The lesion involves the front of the torso and back of the torso · this image was taken at an angle · the patient is a female aged 30–39: 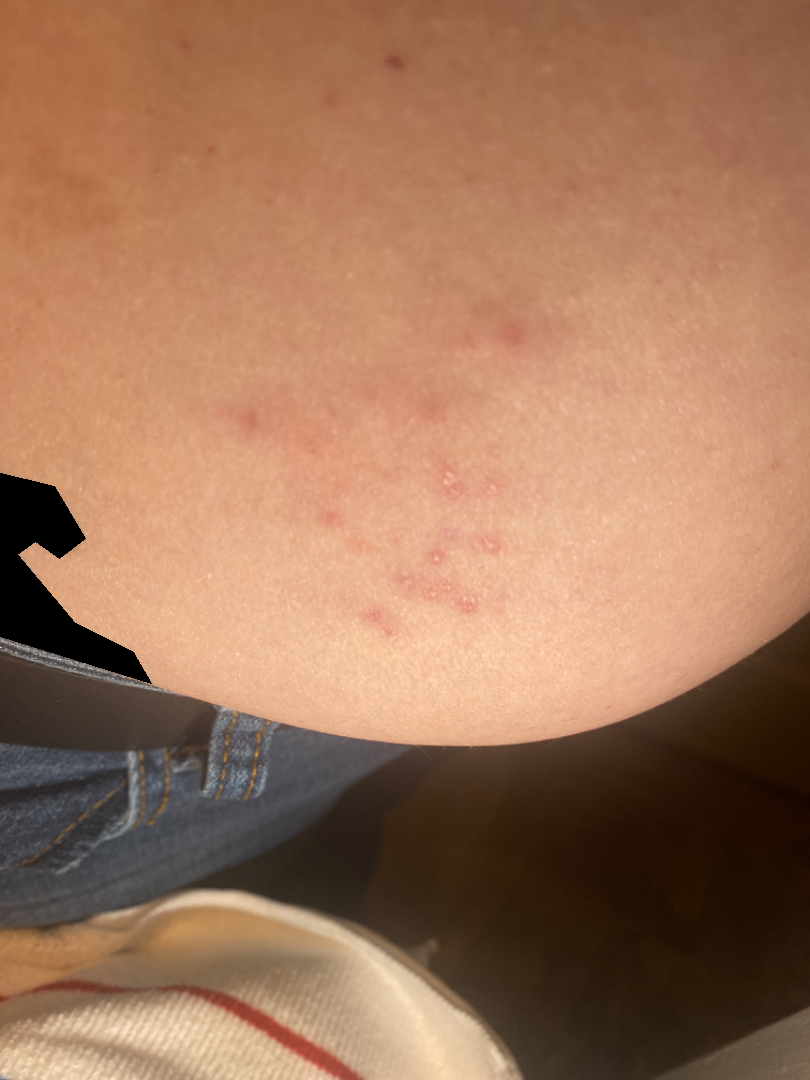Impression:
The condition could not be reliably identified from the image.
History:
Self-categorized by the patient as a rash. Skin tone: FST III; human graders estimated MST 2–3. The patient reports itching. The patient reports the condition has been present for less than one week.